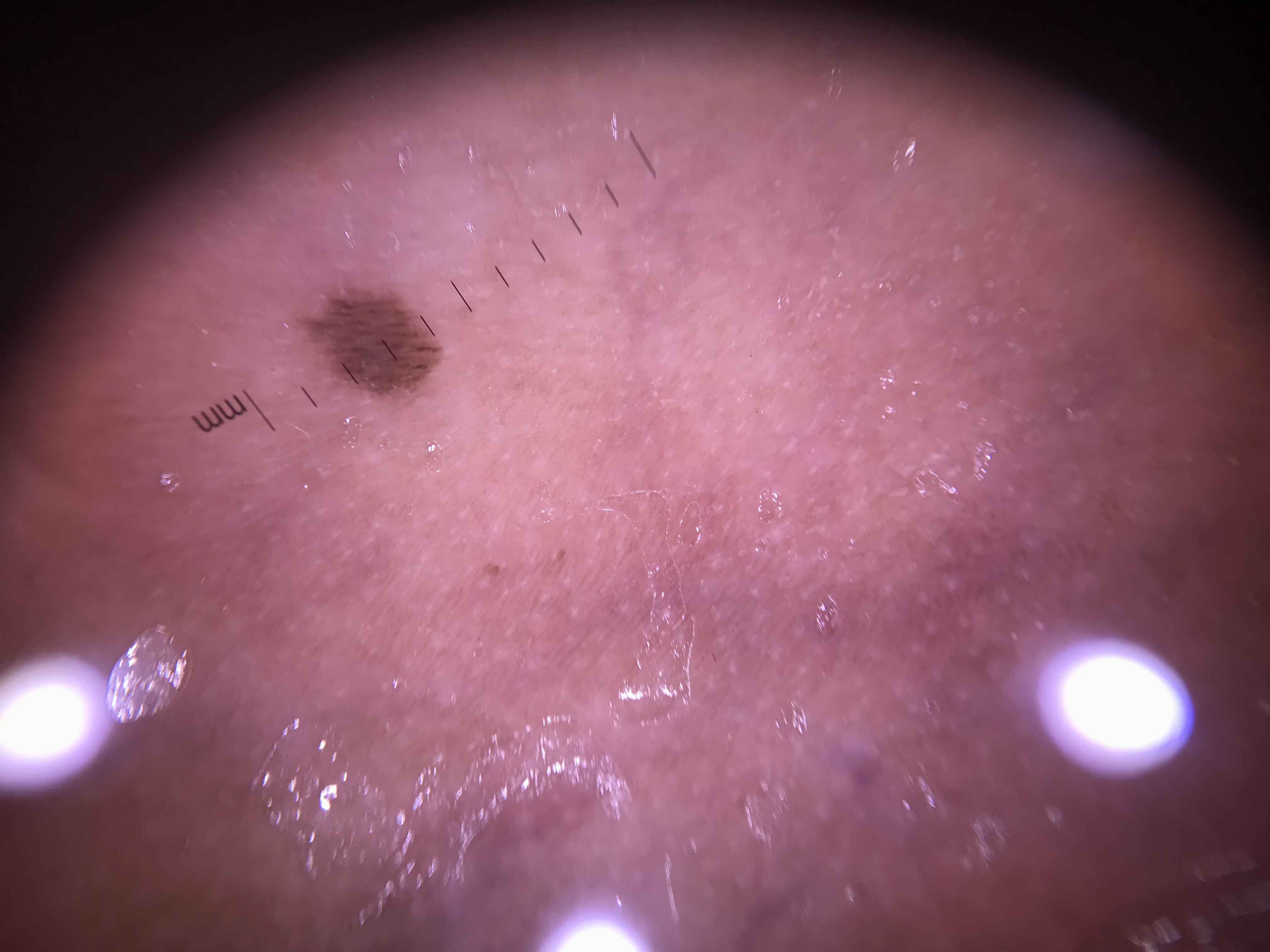imaging — dermatoscopy | lesion type — banal | label — junctional nevus (expert consensus).